The photograph is a close-up of the affected area · skin tone: Fitzpatrick skin type IV:
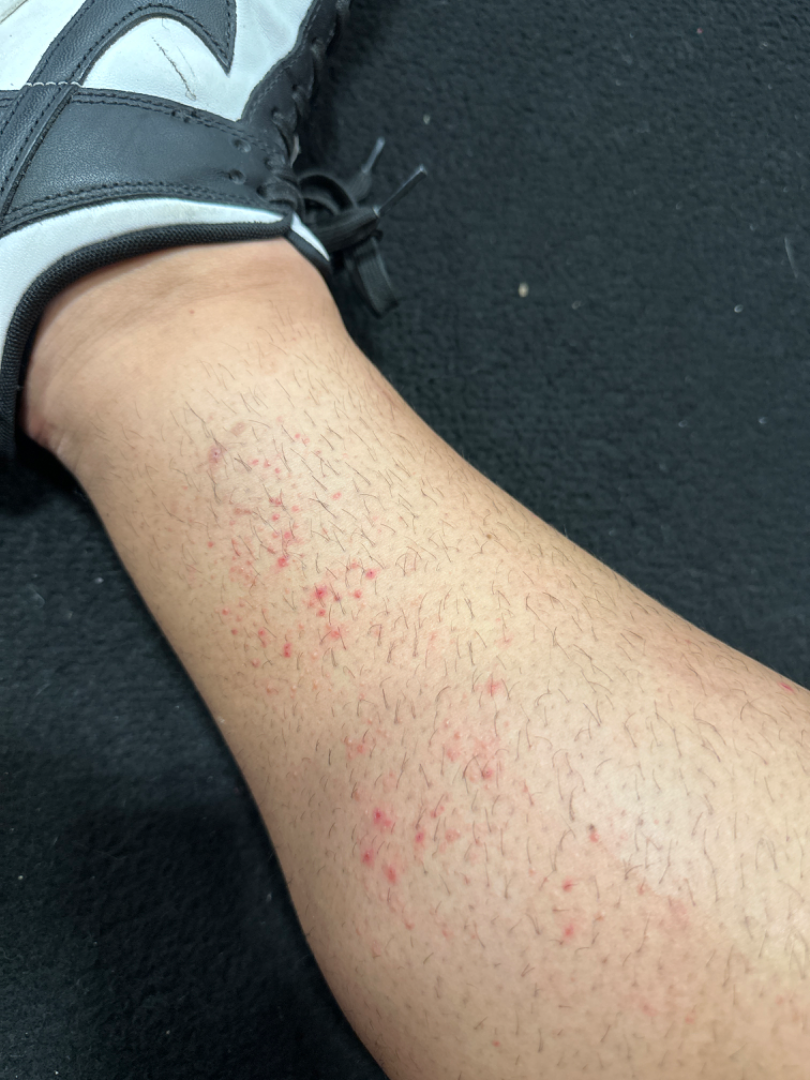assessment: indeterminate from the photograph.